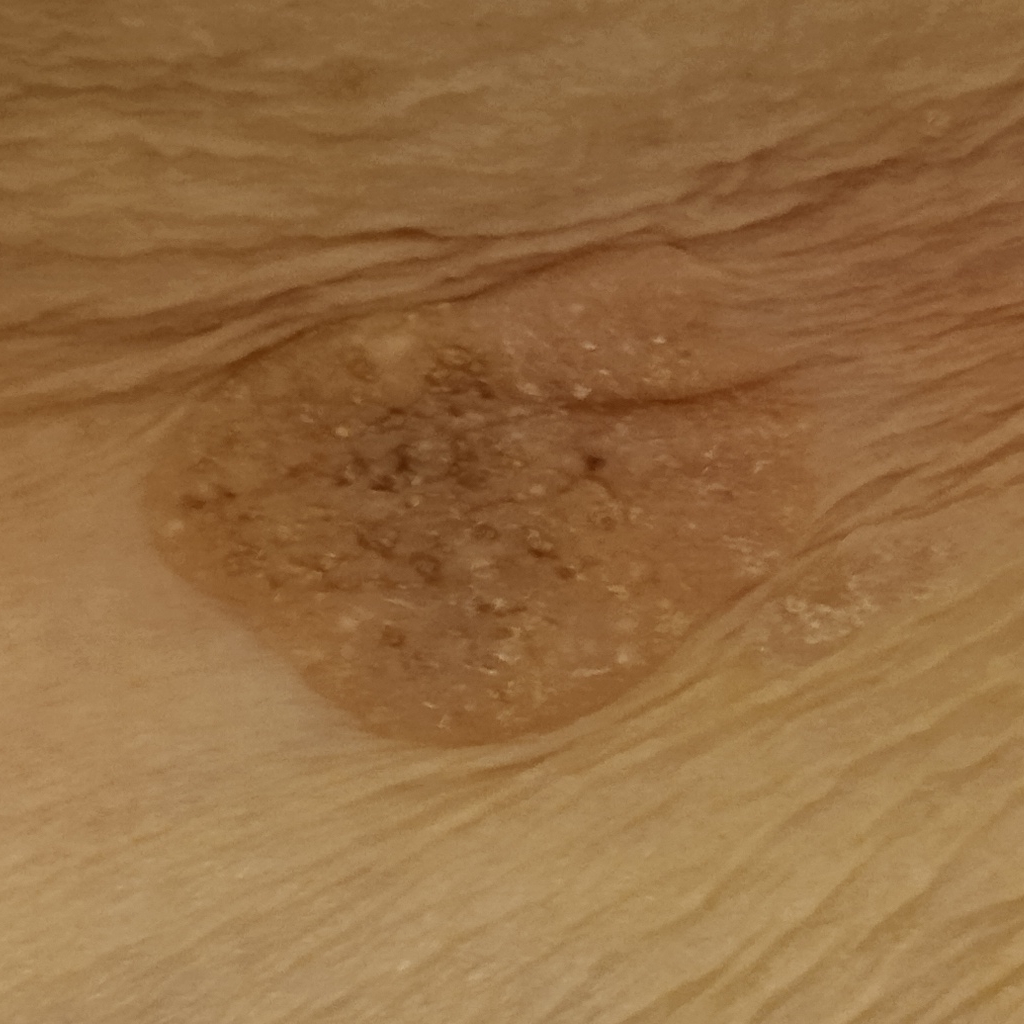Findings: A moderate number of moles by the patient's own estimate. A clinical close-up of a skin lesion. Collected as part of a research study, without a referral diagnosis. Impression: The lesion was assessed as a seborrheic keratosis.